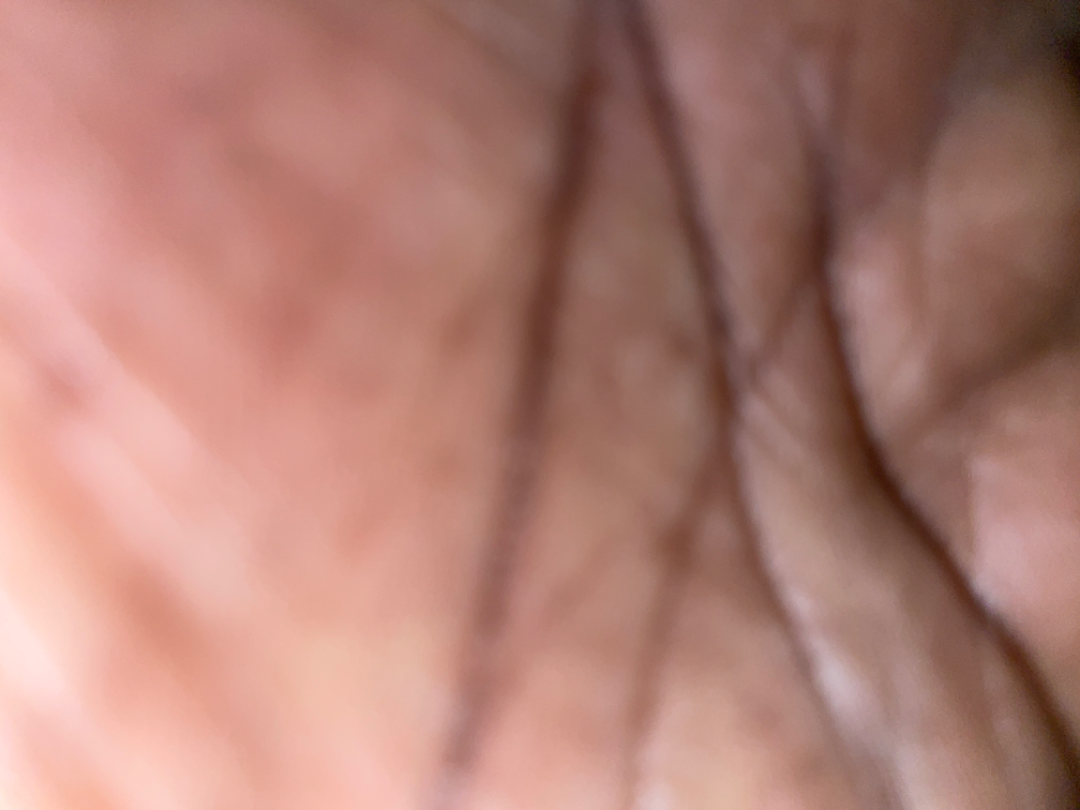<dermatology_case>
<assessment>indeterminate</assessment>
</dermatology_case>